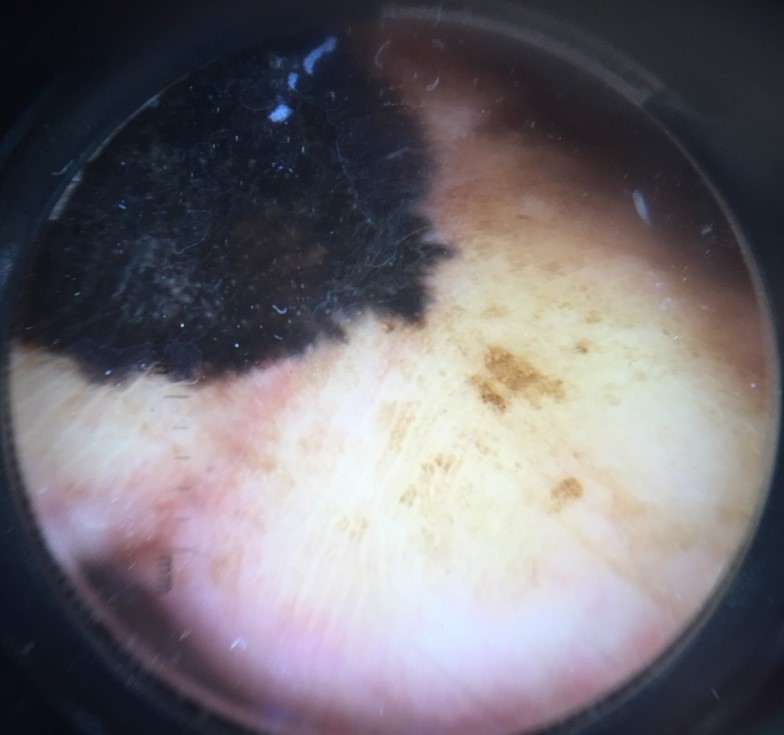Summary: A dermoscopy image of a single skin lesion. Pathology: The biopsy diagnosis was a malignant lesion — an acral lentiginous melanoma.